The patient was assessed as Fitzpatrick skin type III. A female patient in their early 60s. The chart notes prior malignancy (patient or family). A clinical close-up photograph of a skin lesion.
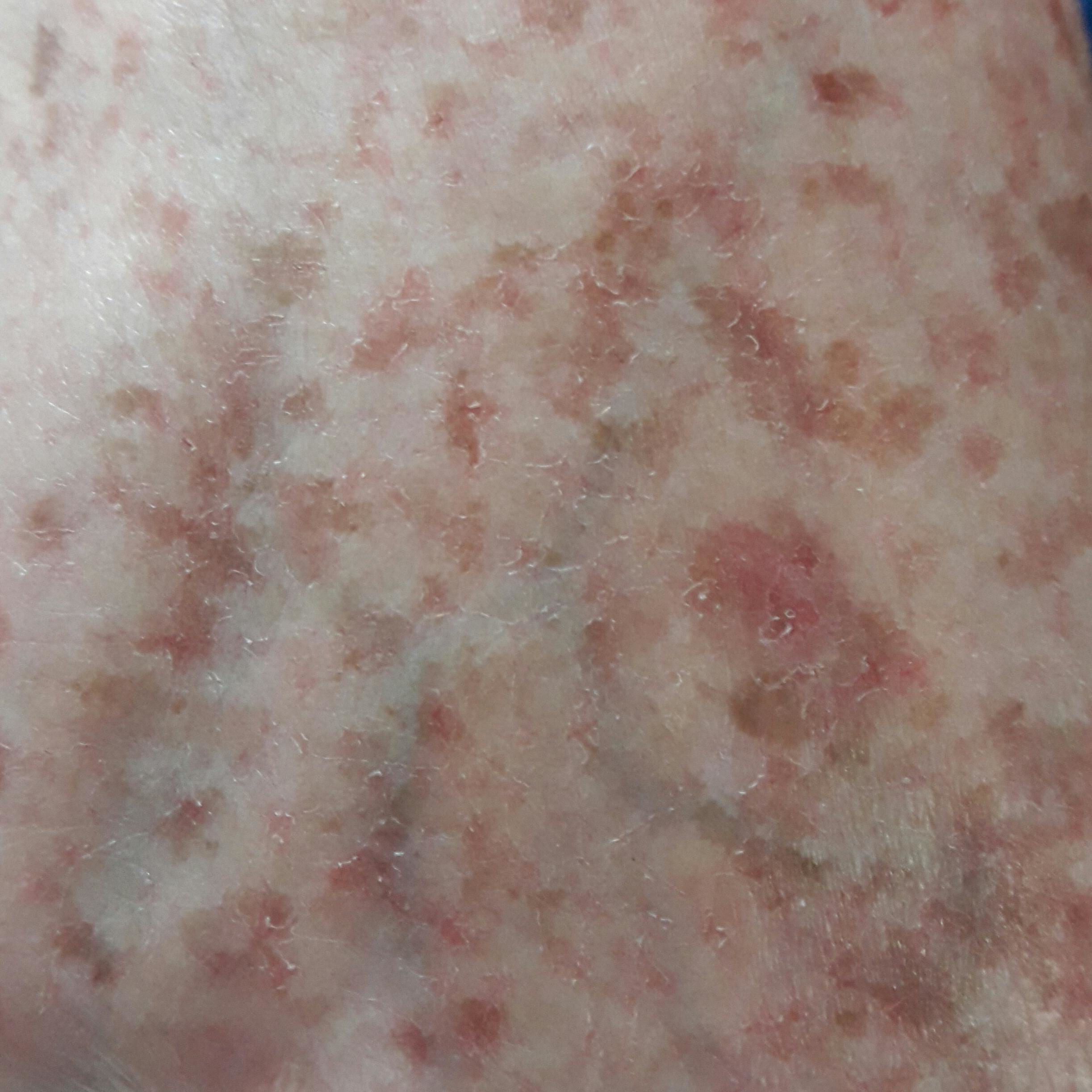Q: What is the anatomic site?
A: a hand
Q: How large is the lesion?
A: approx. 6 × 4 mm
Q: What symptoms does the patient report?
A: itching
Q: What was the clinical impression?
A: actinic keratosis (clinical consensus)